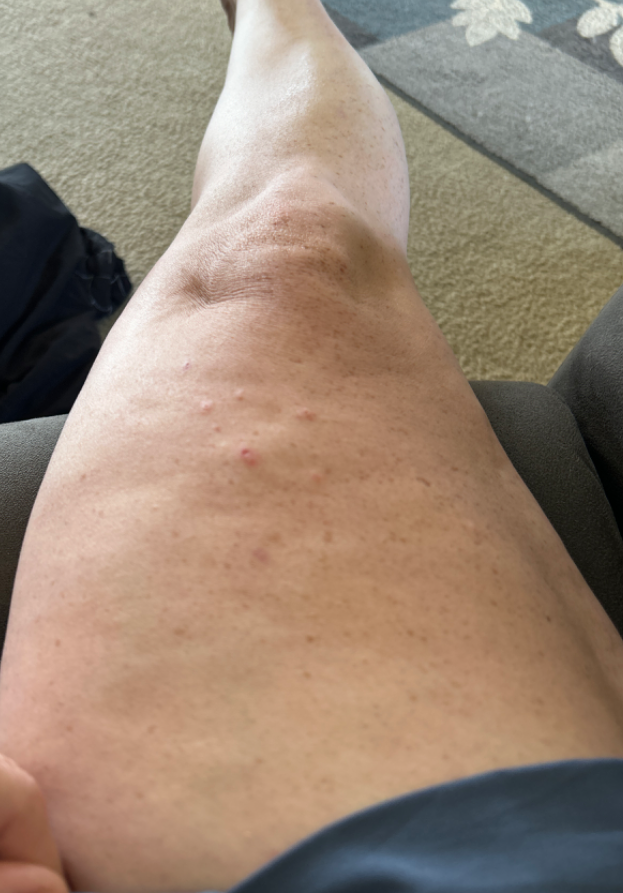| feature | finding |
|---|---|
| texture | raised or bumpy |
| patient describes the issue as | a rash |
| symptoms | itching |
| affected area | arm and leg |
| image framing | at a distance |
| dermatologist impression | Prurigo nodularis (most likely); Folliculitis (considered) |